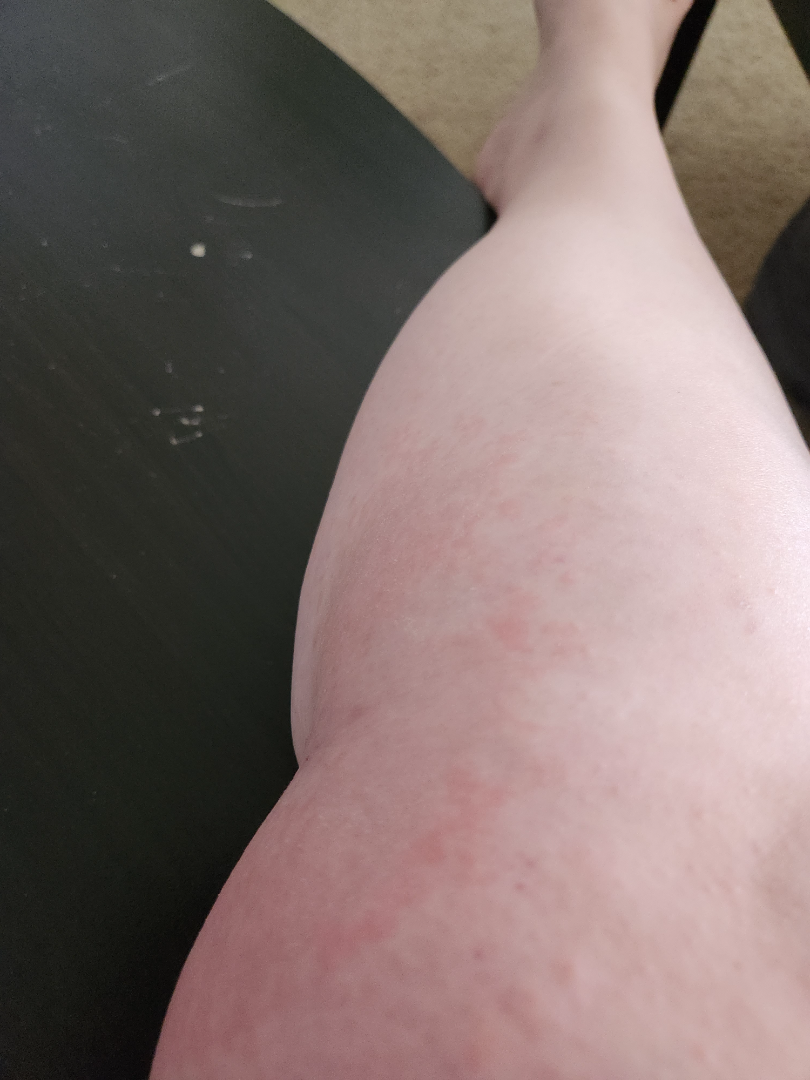body_site: leg
duration: one to four weeks
texture: raised or bumpy
shot_type: at an angle
patient_category: a rash
symptoms:
  - itching
  - enlargement
differential:
  leading:
    - Eczema
  unlikely:
    - Urticaria
    - Allergic Contact Dermatitis